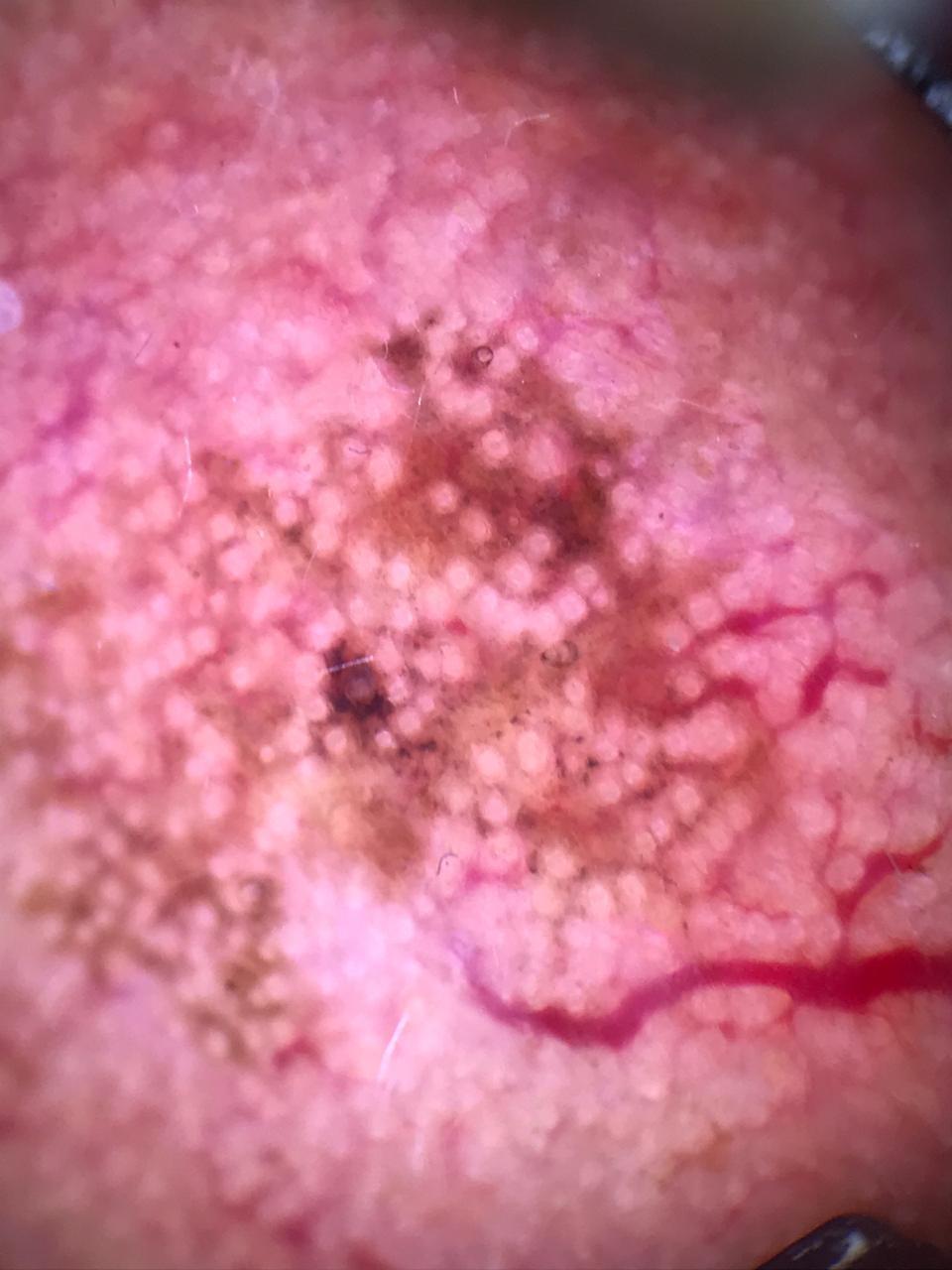Clinical context: A male patient aged approximately 75. Recorded as FST II. Pathology: On biopsy, the diagnosis was a squamous cell carcinoma.